The subject is 30–39, female. This is a close-up image — 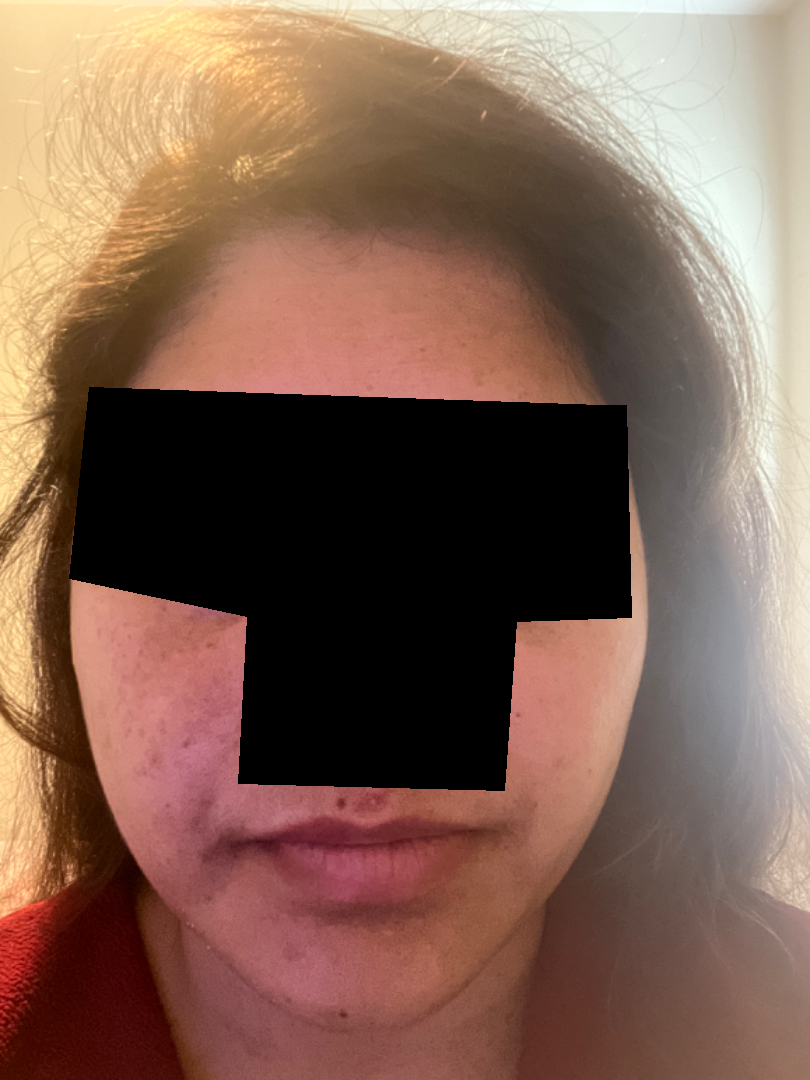The leading consideration is Acne; possibly Perioral Dermatitis.